The lesion involves the arm, close-up view, the contributor is female:
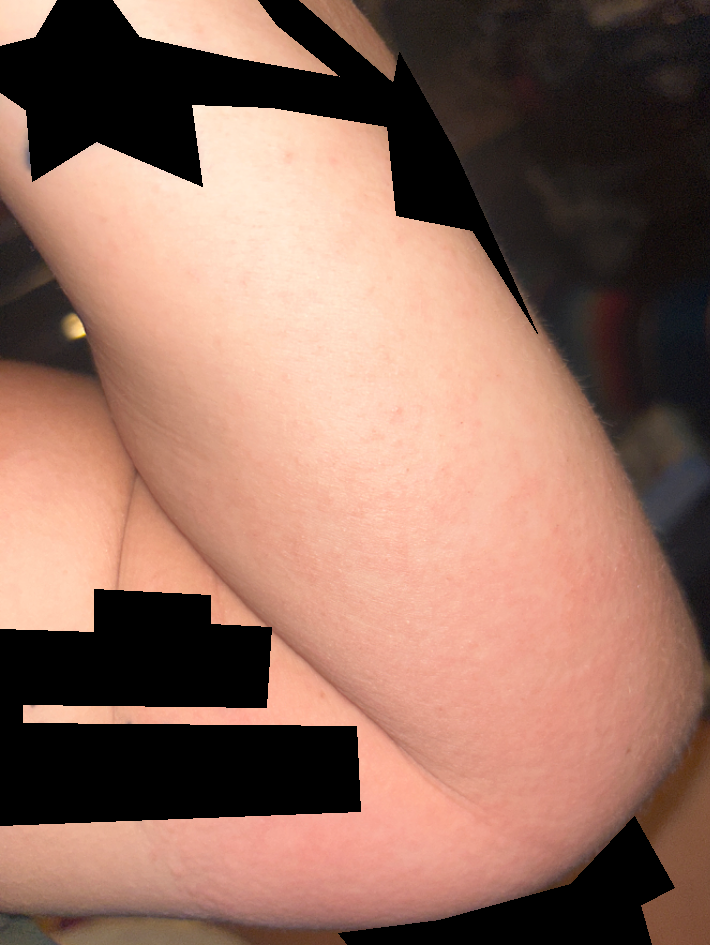– assessment: the differential is split between Urticaria, Eczema and Allergic Contact Dermatitis